The lesion is associated with itching and bothersome appearance; texture is reported as fluid-filled; the patient considered this a rash; skin tone: Fitzpatrick phototype II; an image taken at an angle; female patient, age 40–49; the condition has been present for about one day — 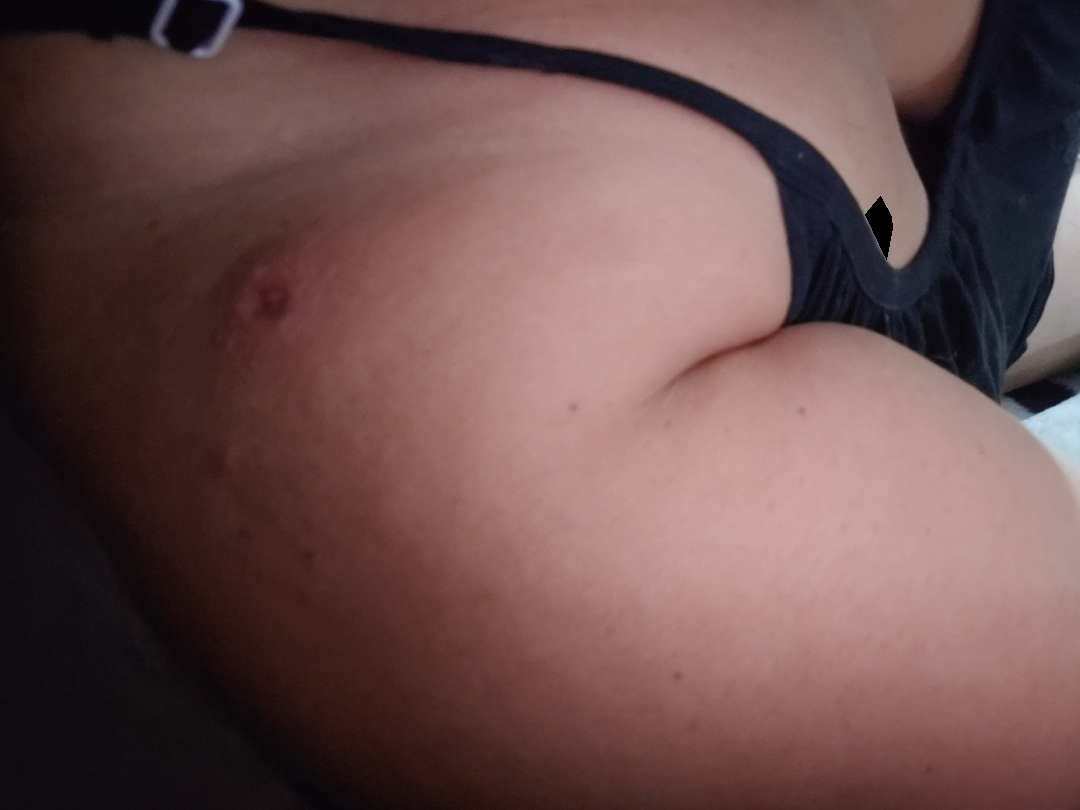The image was not sufficient for the reviewer to characterize the skin condition.